The patient is a male aged approximately 55, a dermoscopy image of a single skin lesion.
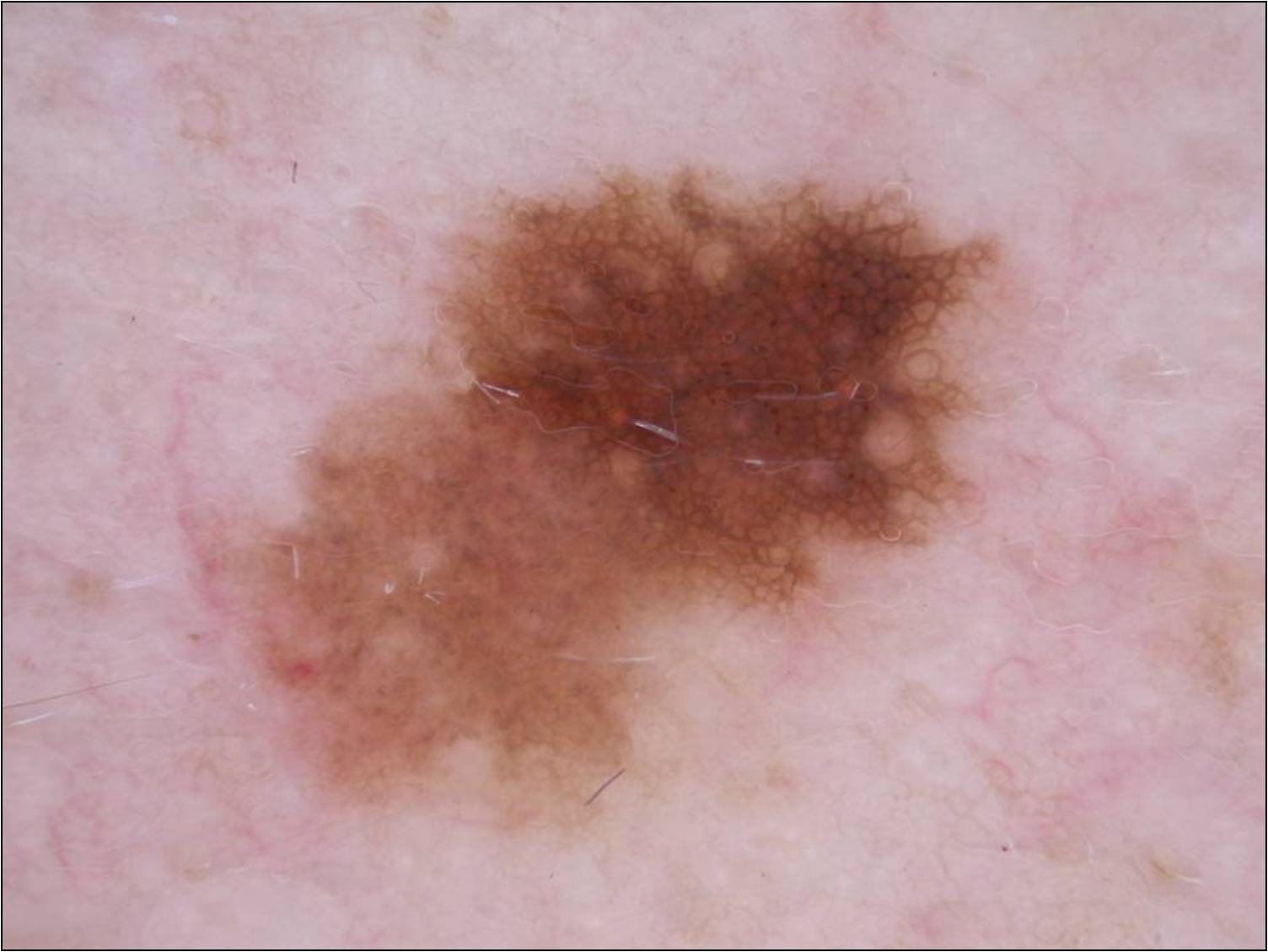Dermoscopic examination shows pigment network. The lesion is located at x1=179 y1=162 x2=1018 y2=833. Clinically diagnosed as a melanocytic nevus, a benign skin lesion.